An image taken at an angle. Located on the arm. The patient is a female aged 50–59:
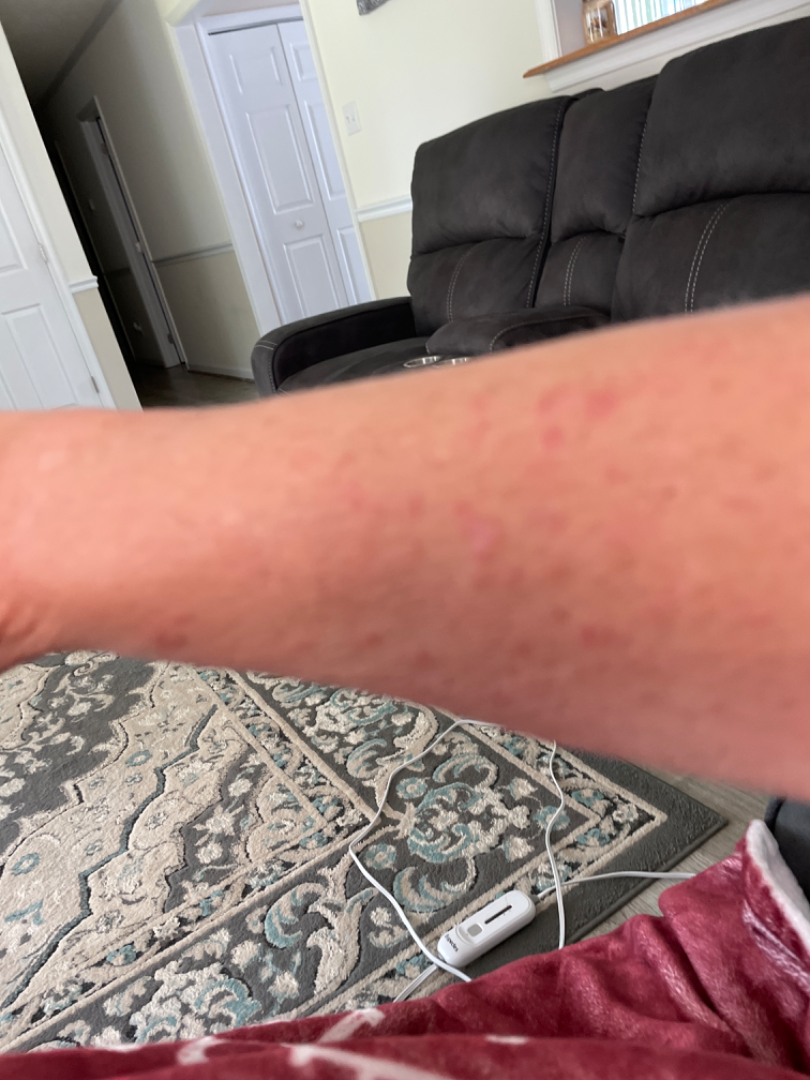Notes:
* assessment — indeterminate
* patient describes the issue as — a rash
* symptoms — itching
* skin tone — Fitzpatrick phototype II
* systemic symptoms — none reported
* symptom duration — one to four weeks